The photo was captured at an angle. Texture is reported as fluid-filled and raised or bumpy. The head or neck, top or side of the foot and leg are involved. The patient described the issue as a rash. The lesion is associated with bothersome appearance, pain, itching and burning: 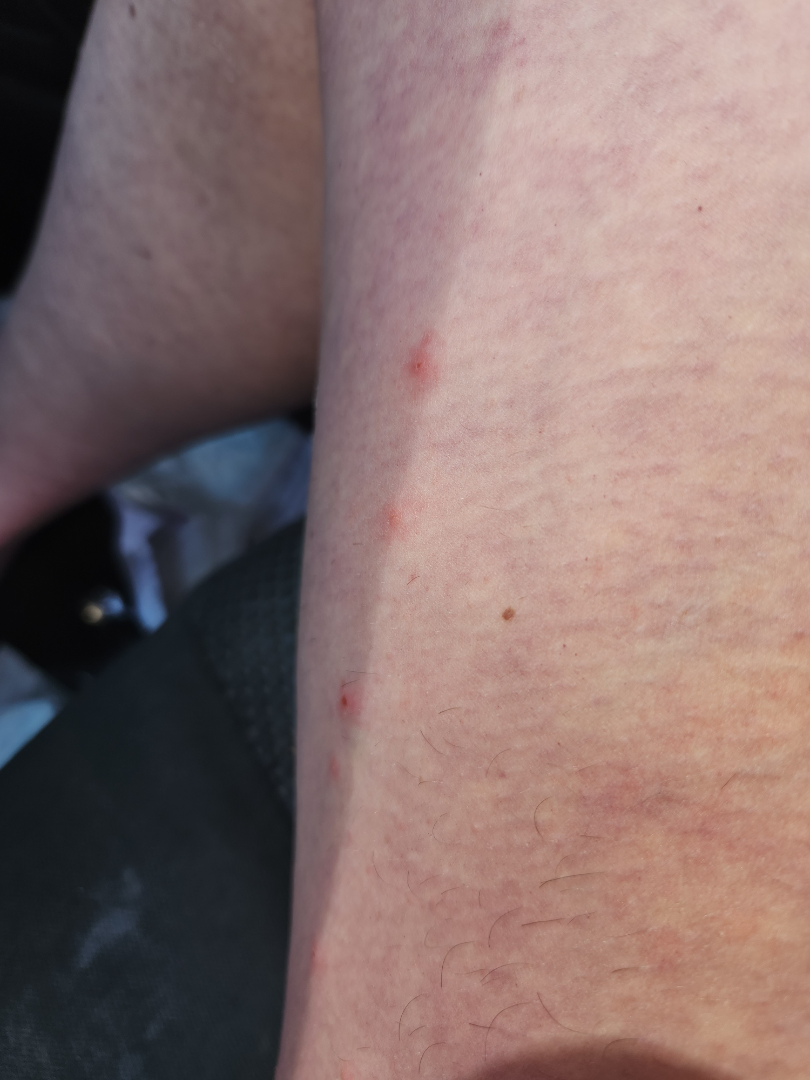Assessment: The dermatologist could not determine a likely condition from the photograph alone.